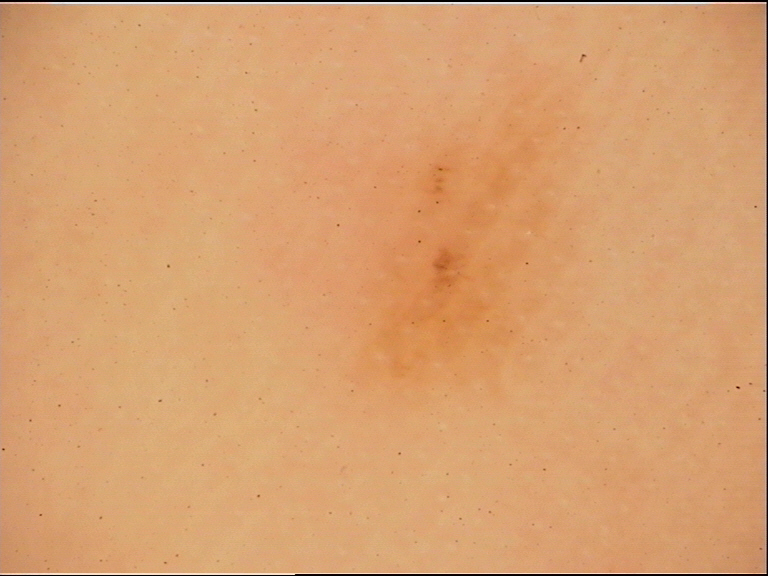A dermoscopic image of a skin lesion. The morphology is that of a banal lesion. The diagnosis was an acral junctional nevus.